A female patient aged approximately 50. A skin lesion imaged with a dermatoscope.
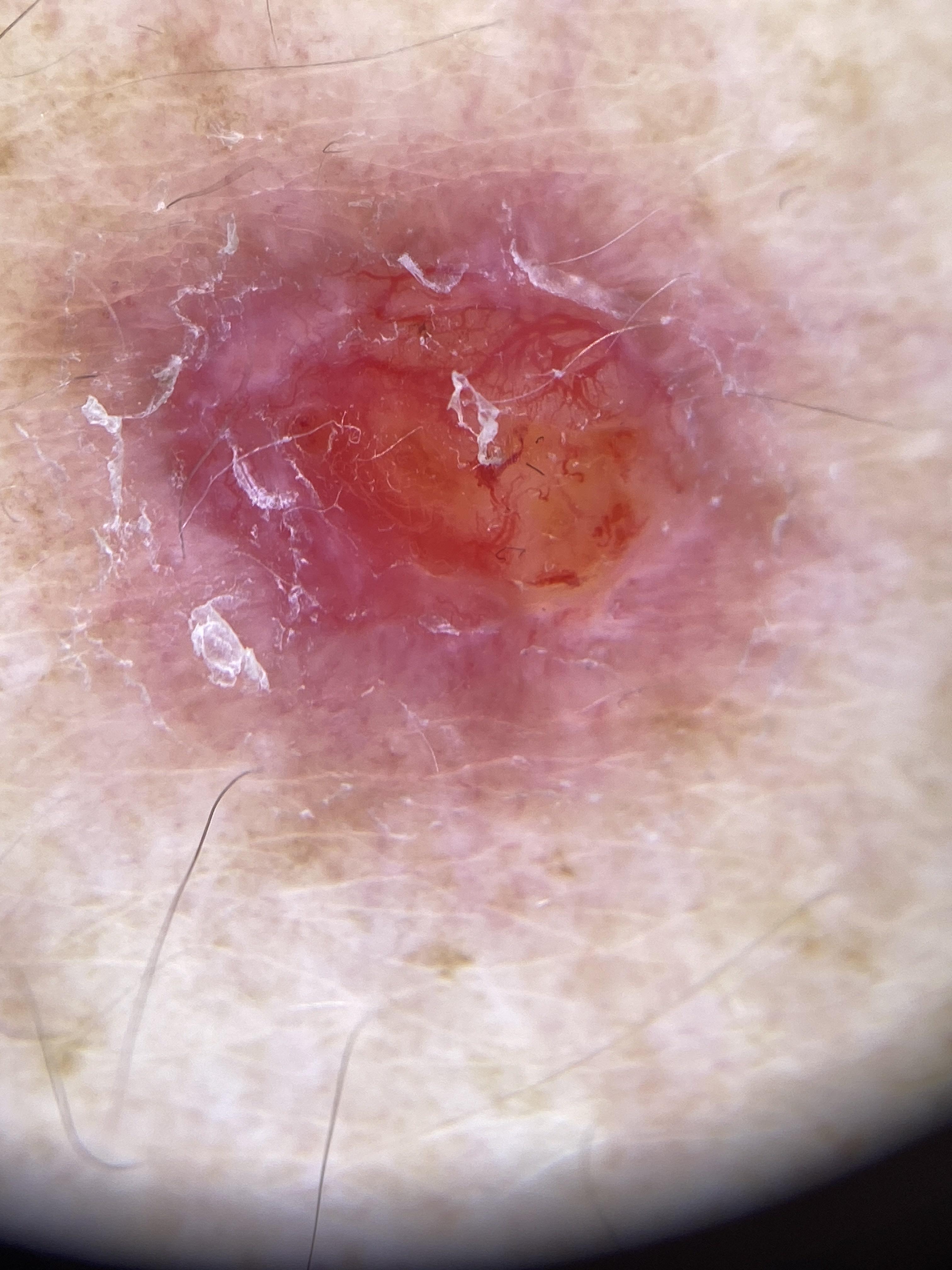anatomic site: an upper extremity | diagnosis: Basal cell carcinoma (biopsy-proven).